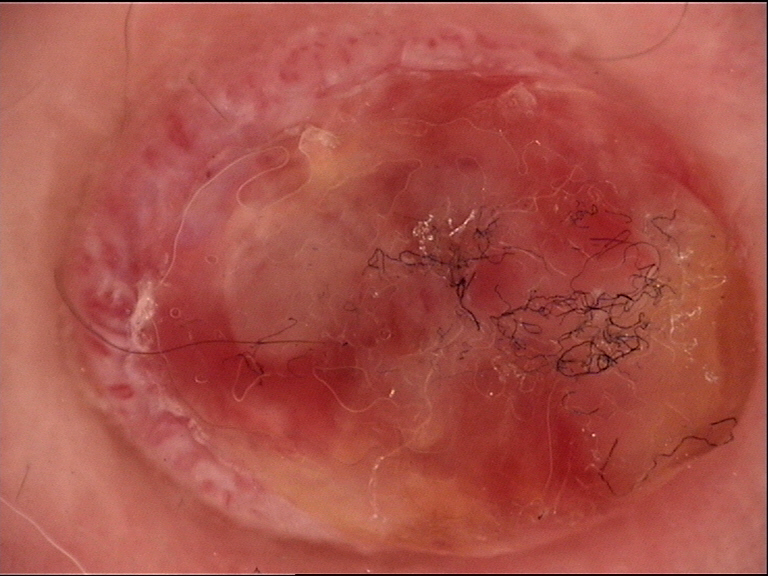Diagnosis:
Confirmed on histopathology as a Kaposi sarcoma.